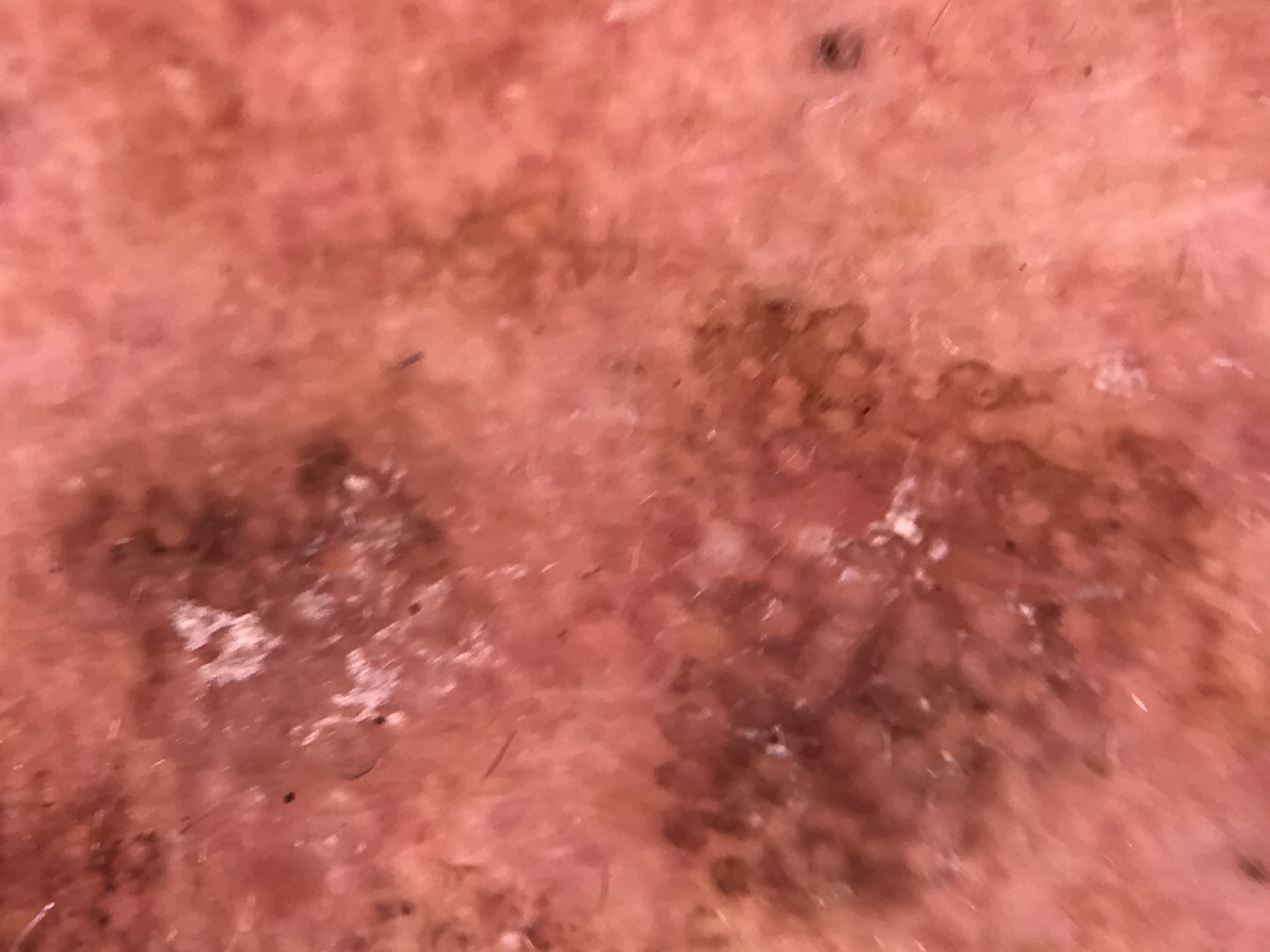| feature | finding |
|---|---|
| class | actinic keratosis (expert consensus) |